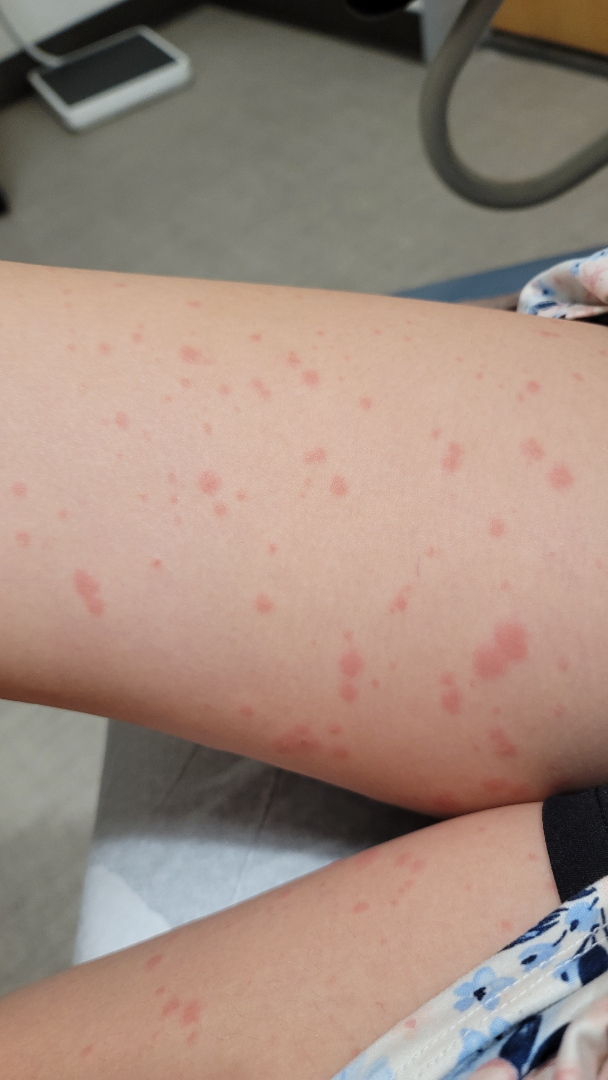Background: The contributor notes the lesion is flat. Self-categorized by the patient as a rash. A close-up photograph. The affected area is the arm, back of the torso and leg. Female contributor, age 18–29. Present for about one day. Findings: On photographic review, the differential is split between Viral Exanthem and Drug Rash.